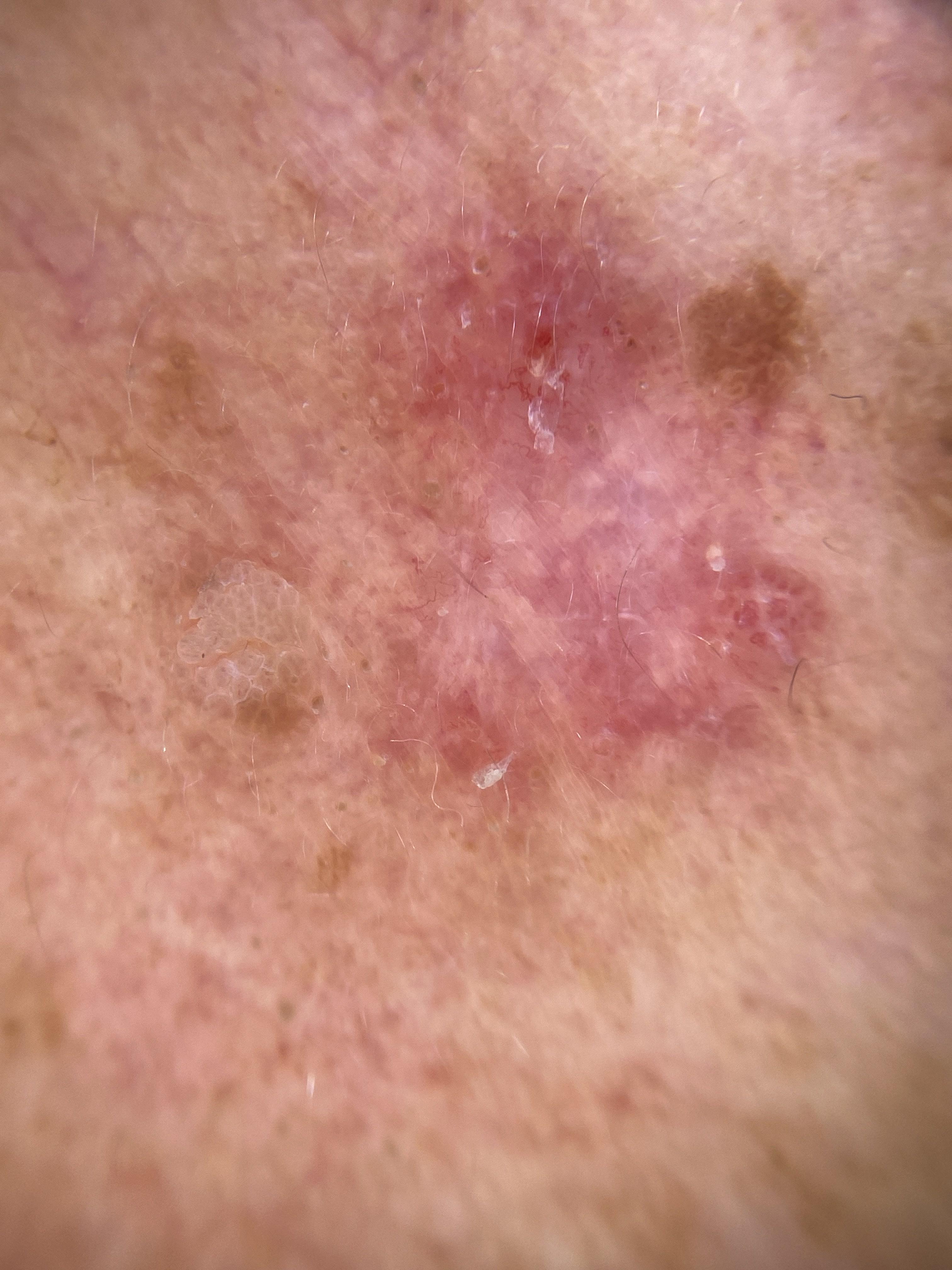* diagnostic label: Basal cell carcinoma (biopsy-proven)